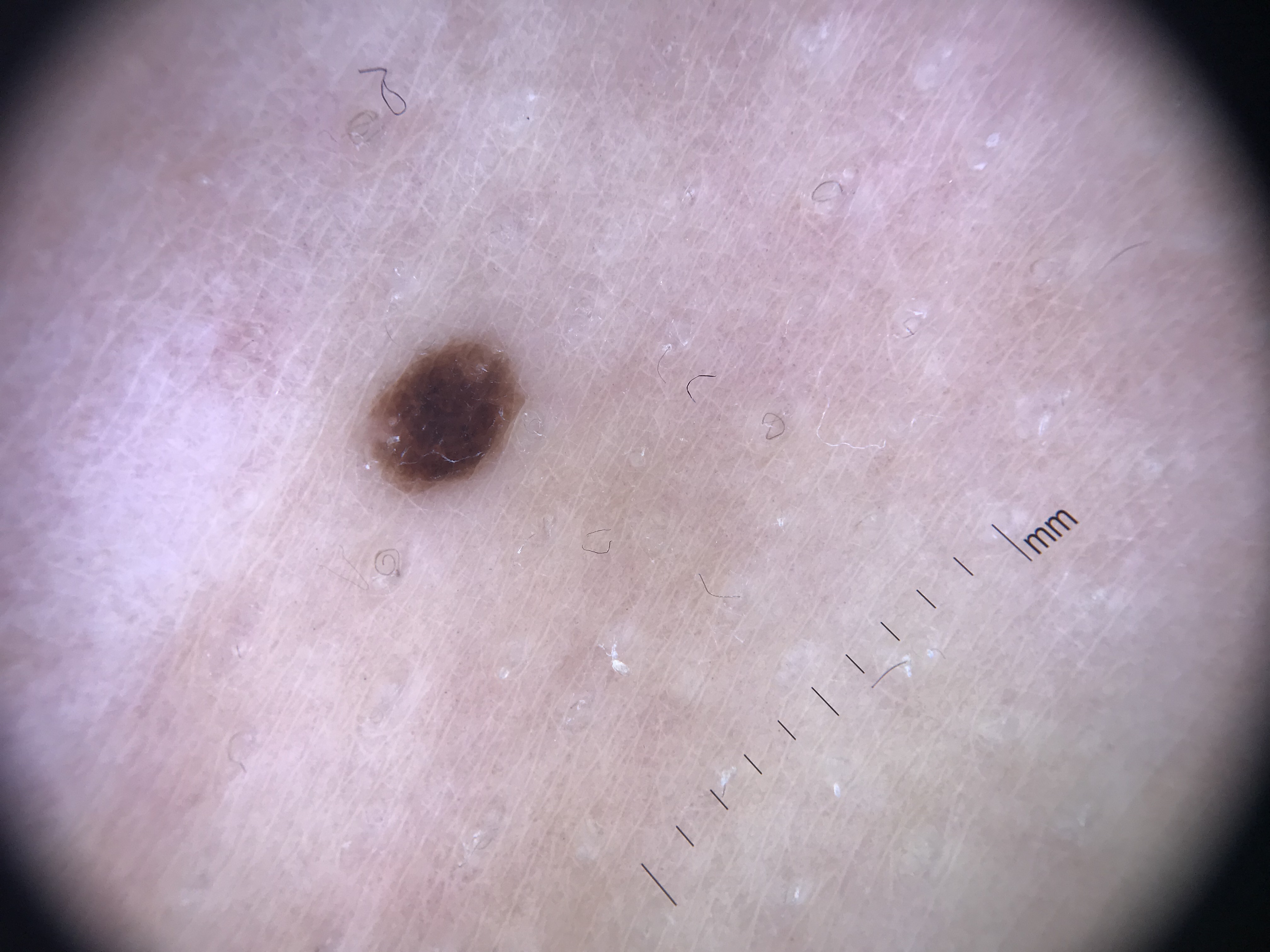A skin lesion imaged with a dermatoscope. Consistent with a banal lesion — a junctional nevus.